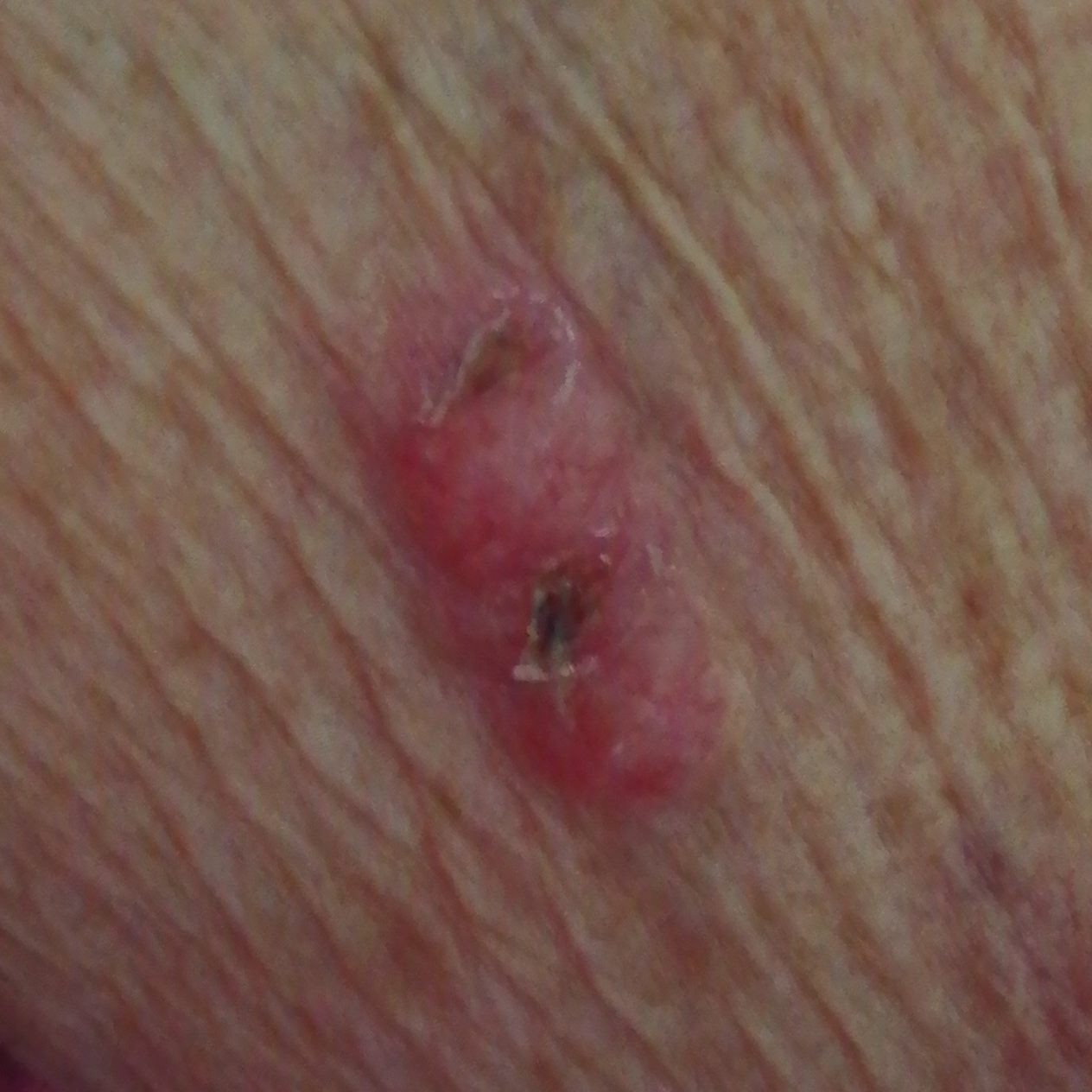Q: What is the patient's skin type?
A: II
Q: What is the imaging modality?
A: clinical photograph
Q: Patient demographics?
A: female, in their early 70s
Q: Any relevant history?
A: tobacco use
Q: What is the anatomic site?
A: an arm
Q: How large is the lesion?
A: approx. 18 × 8 mm
Q: What does the patient describe?
A: itching, elevation, bleeding, growth, change in appearance / no pain
Q: What is this lesion?
A: basal cell carcinoma (biopsy-proven)